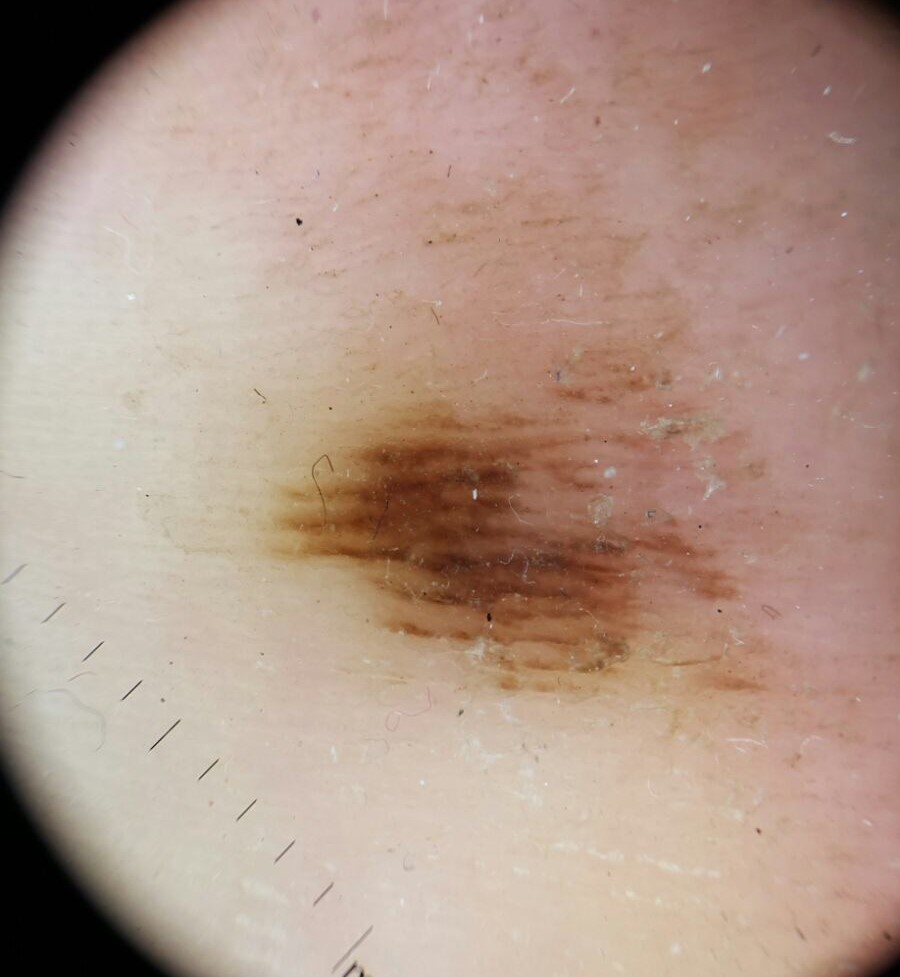modality: dermoscopy; label: acral dysplastic junctional nevus (expert consensus).